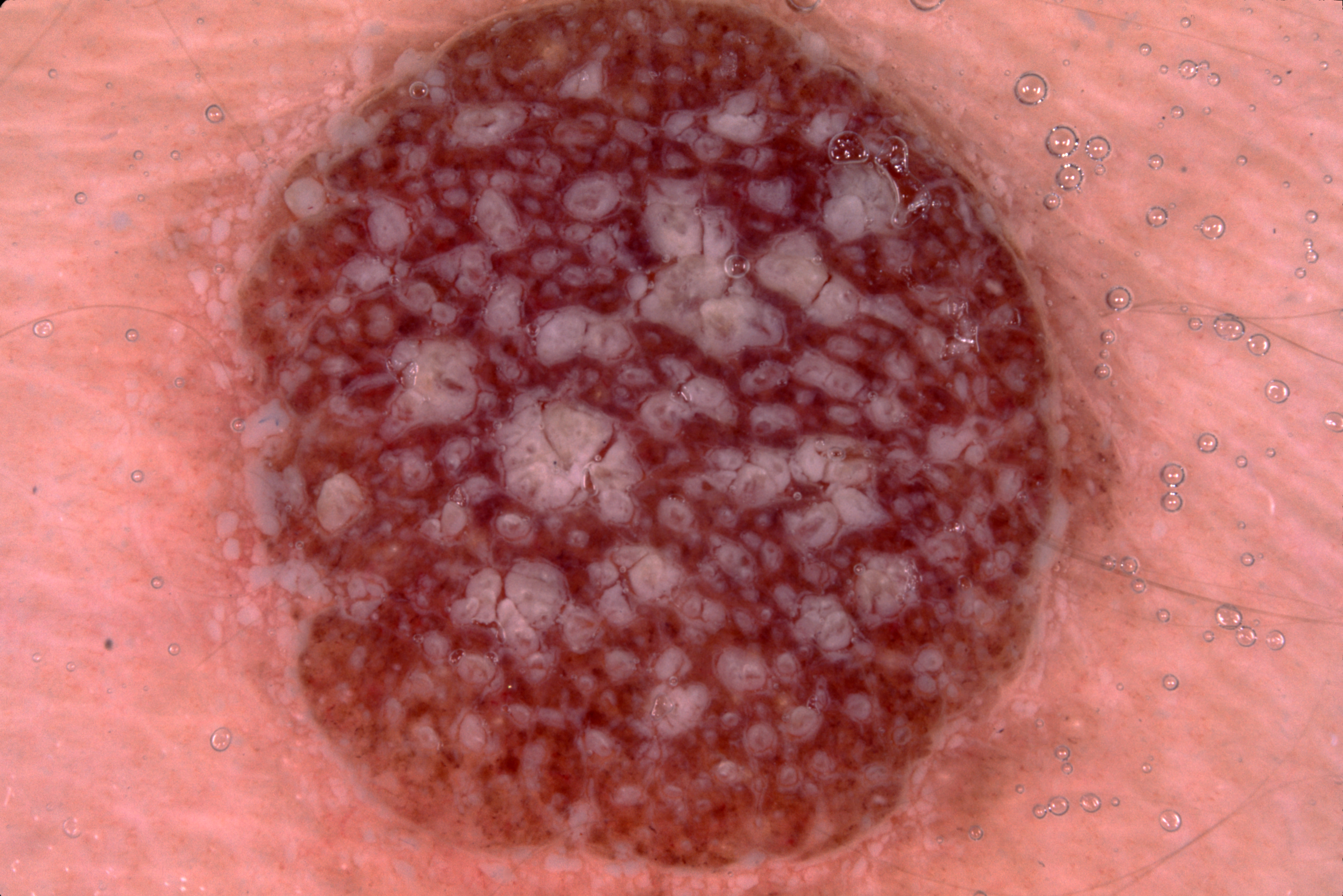Image and clinical context: A dermoscopic image of a skin lesion. The patient is a female approximately 25 years of age. In (x1, y1, x2, y2) order, lesion location: 232 0 1121 895. Dermoscopic assessment notes no negative network, streaks, pigment network, or milia-like cysts. The lesion is clipped by the edge of the image. The lesion takes up a large portion of the image. Conclusion: The diagnostic assessment was a melanocytic nevus, a benign lesion.